The patient is 30–39, female · an image taken at an angle · the affected area is the leg, arm, head or neck and back of the hand — 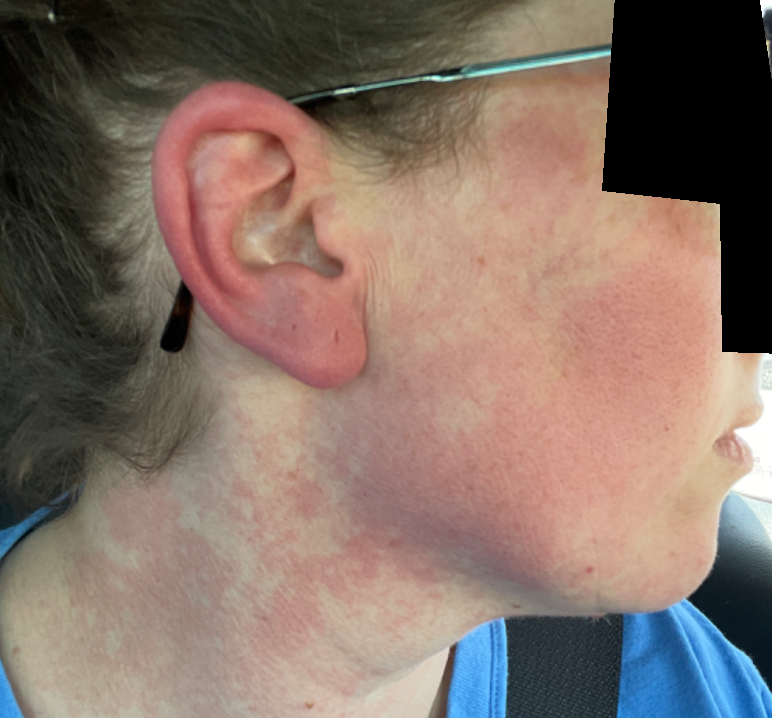reported symptoms: enlargement, burning and itching
history: about one day
self-categorized as: a rash
impression: Allergic Contact Dermatitis (leading); Rosacea (possible); Irritant Contact Dermatitis (remote)